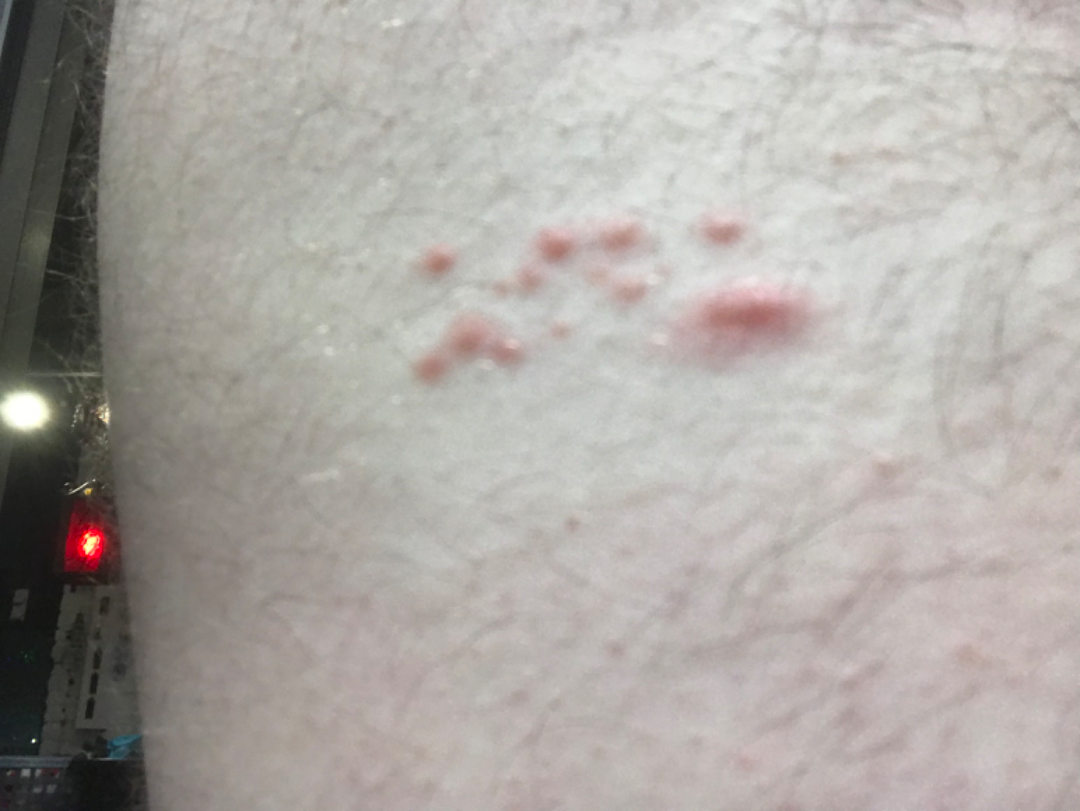Q: What was the assessment?
A: not assessable
Q: Anatomic location?
A: front of the torso
Q: How long has this been present?
A: less than one week
Q: What is the lesion texture?
A: raised or bumpy
Q: What symptoms does the patient report?
A: itching and burning
Q: Image view?
A: close-up